This is a dermoscopic photograph of a skin lesion.
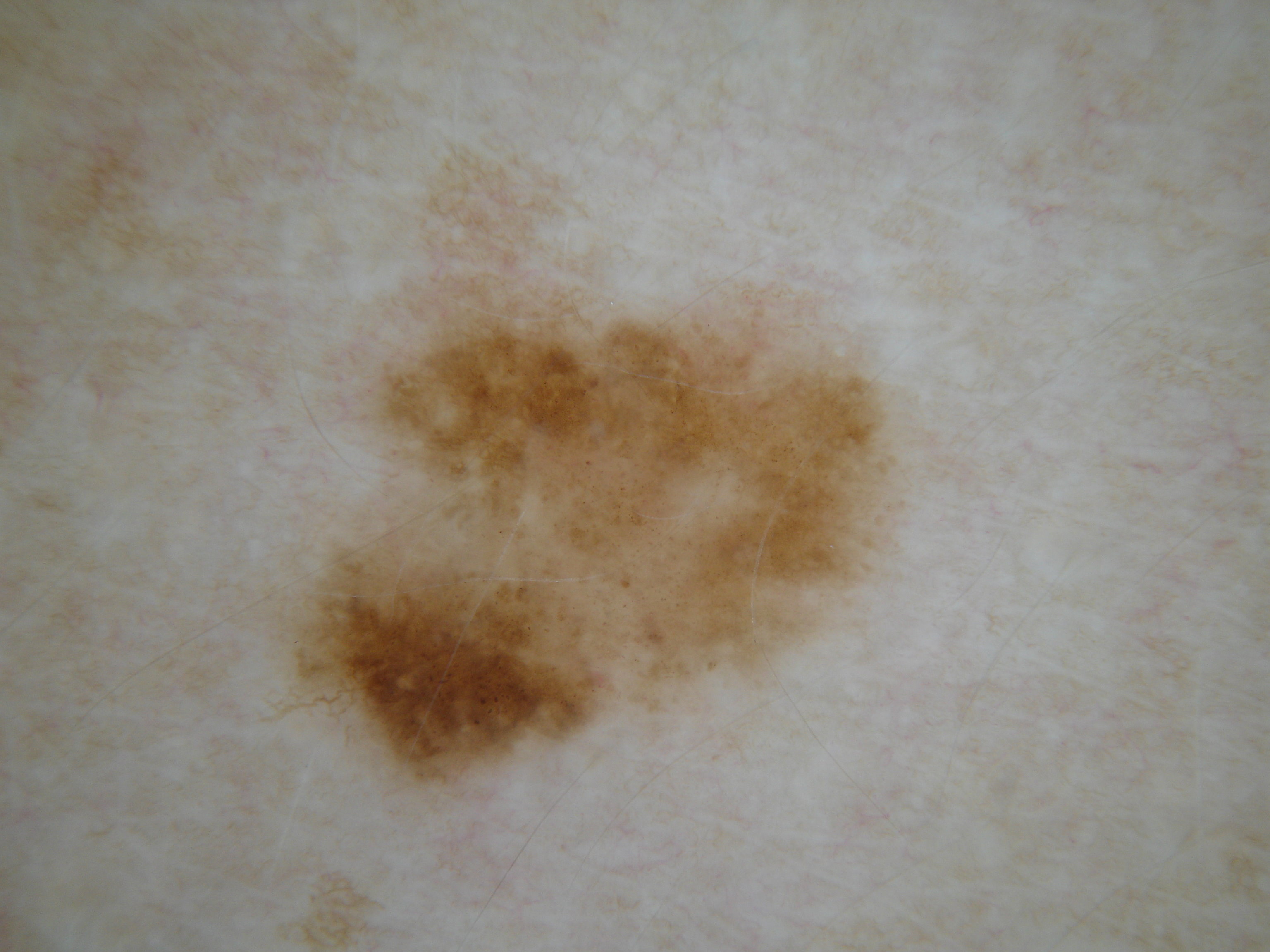{
  "dermoscopic_features": {
    "present": [
      "pigment network",
      "globules"
    ],
    "absent": [
      "milia-like cysts",
      "negative network",
      "streaks"
    ]
  },
  "lesion_extent": {
    "approx_field_fraction_pct": 22
  },
  "lesion_location": {
    "bbox_xyxy": [
      282,
      132,
      906,
      817
    ]
  },
  "diagnosis": {
    "name": "melanocytic nevus",
    "malignancy": "benign",
    "lineage": "melanocytic",
    "provenance": "clinical"
  }
}